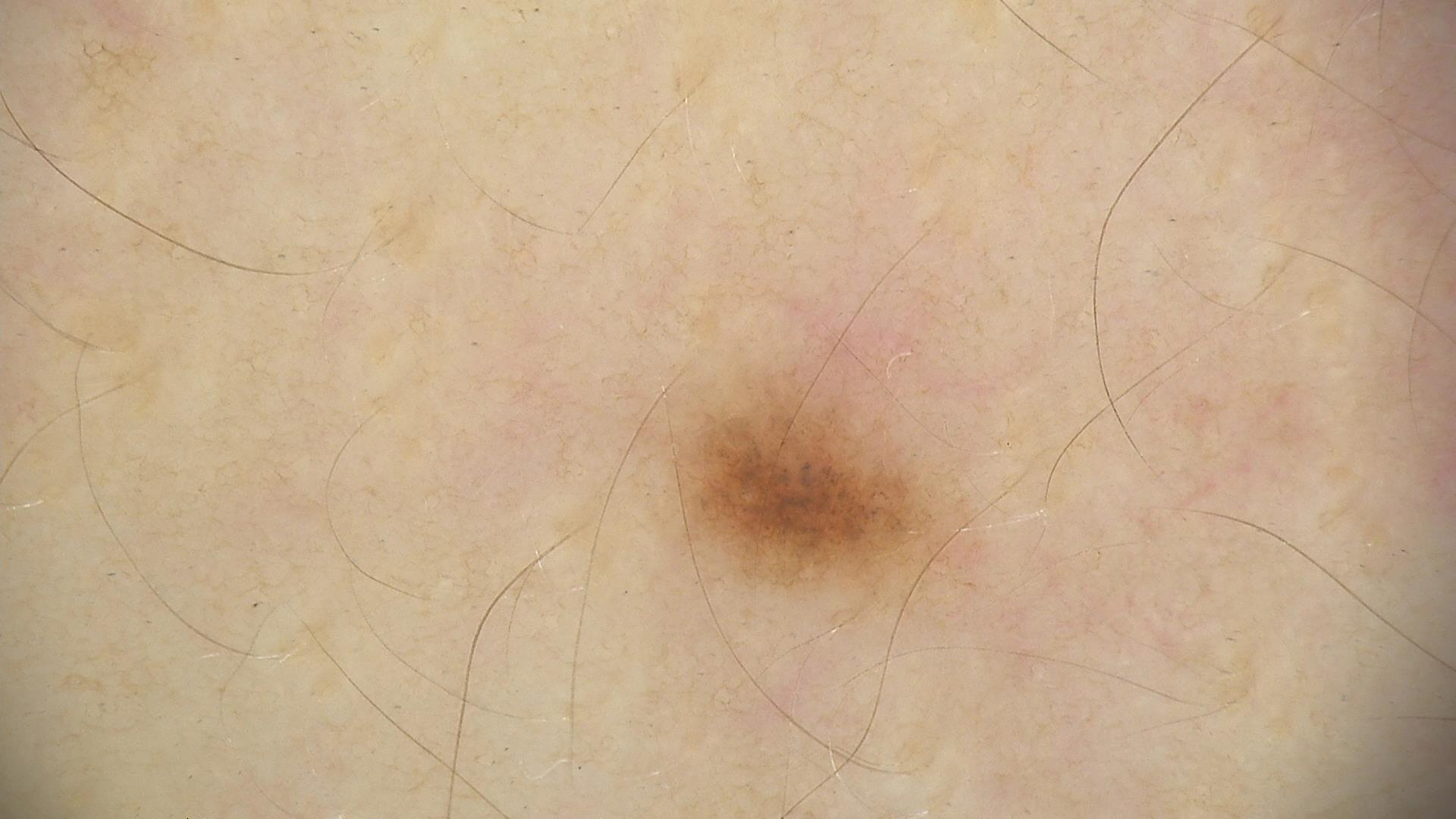Dermoscopy of a skin lesion. Labeled as a dysplastic junctional nevus.